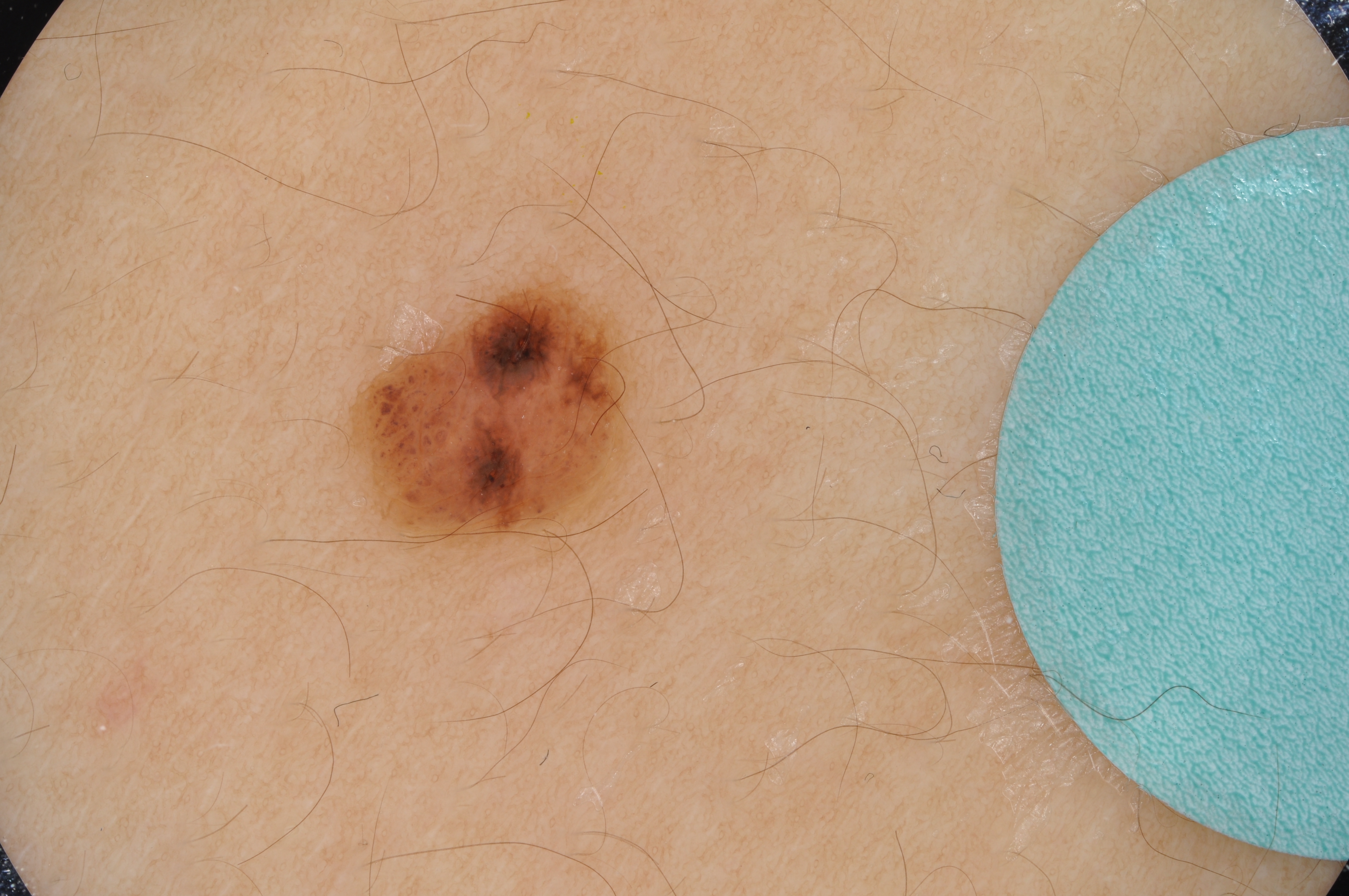This is a dermoscopic photograph of a skin lesion. A female subject, aged 13-17. The dermoscopic pattern shows globules, with no streaks, pigment network, milia-like cysts, or negative network. A small lesion within a wider field of skin. Lesion location: left=331, top=266, right=654, bottom=559. Clinically diagnosed as a melanocytic nevus.